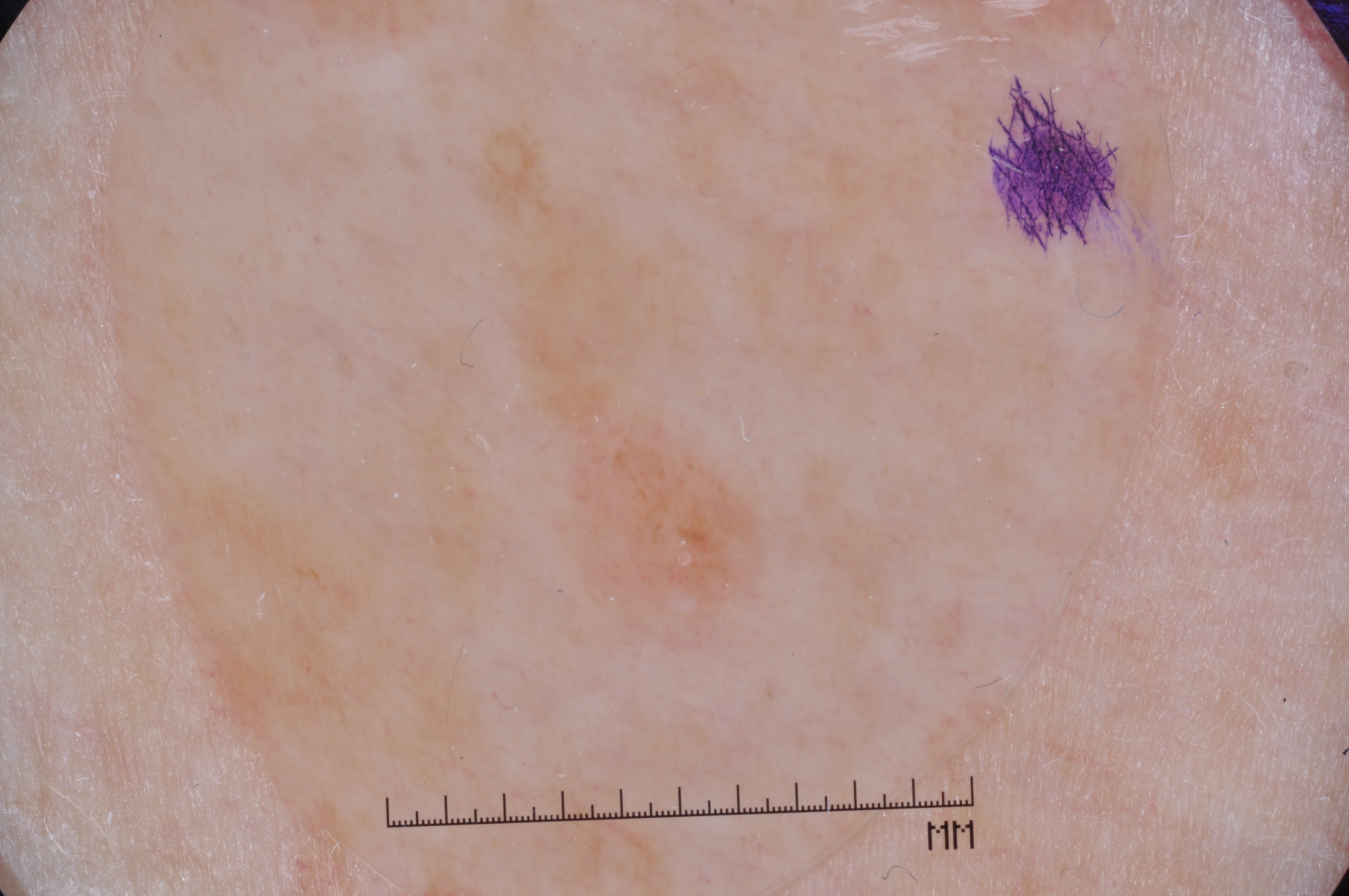Q: How was this image acquired?
A: dermoscopy
Q: Which assessed dermoscopic features were absent?
A: pigment network, milia-like cysts, streaks, and negative network
Q: Where is the lesion located?
A: <bbox>461, 106, 785, 651</bbox>
Q: What did the assessment conclude?
A: a melanocytic nevus